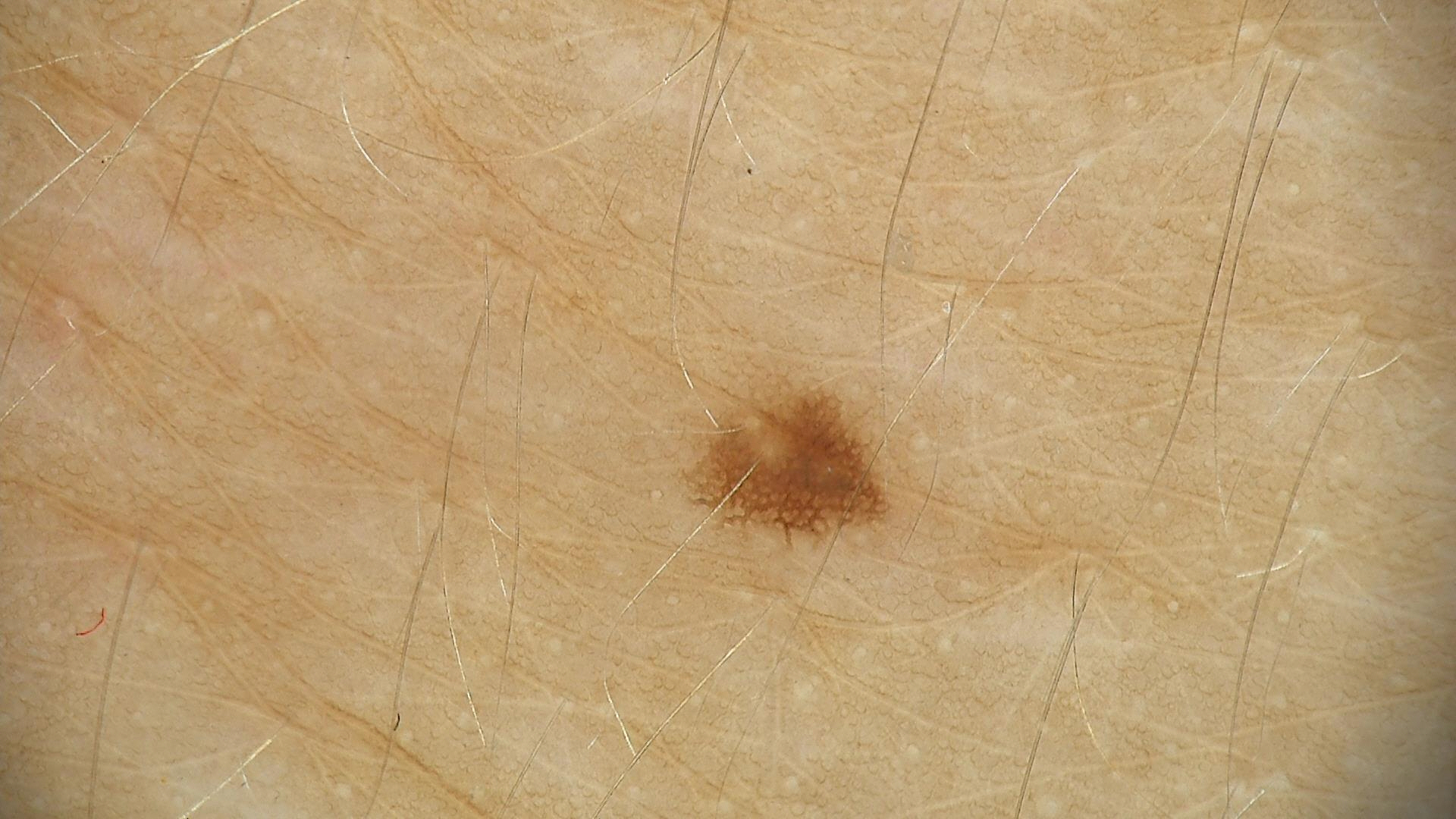– label — dysplastic junctional nevus (expert consensus)